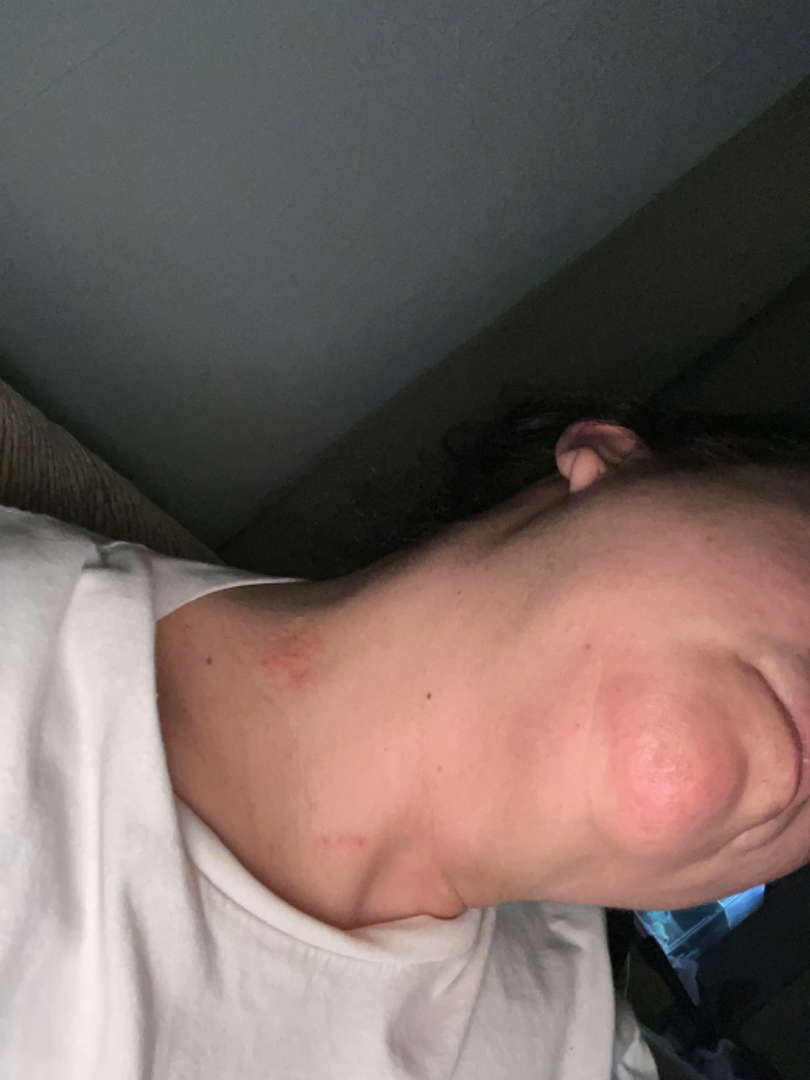body site = head or neck, photo taken = close-up.